The subject is a female aged 18–29, the photograph was taken at an angle — 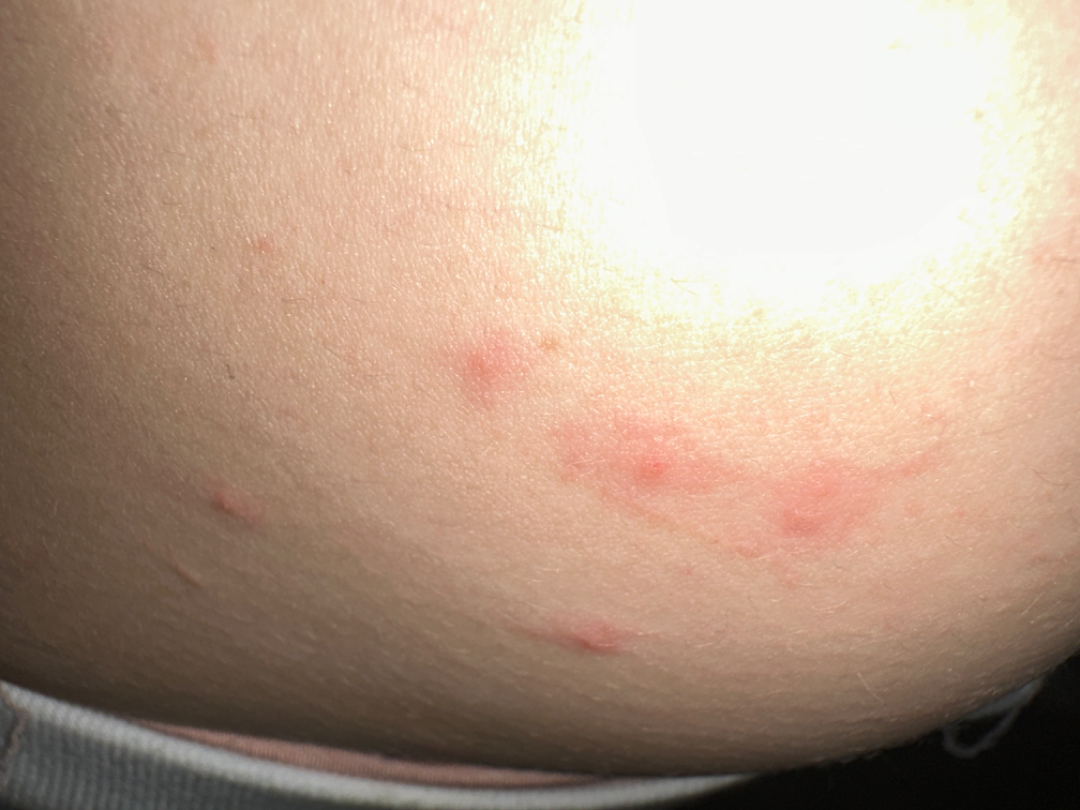Case summary:
– skin tone — Fitzpatrick III
– dermatologist impression — Scabies and Insect Bite were each considered, in no particular order